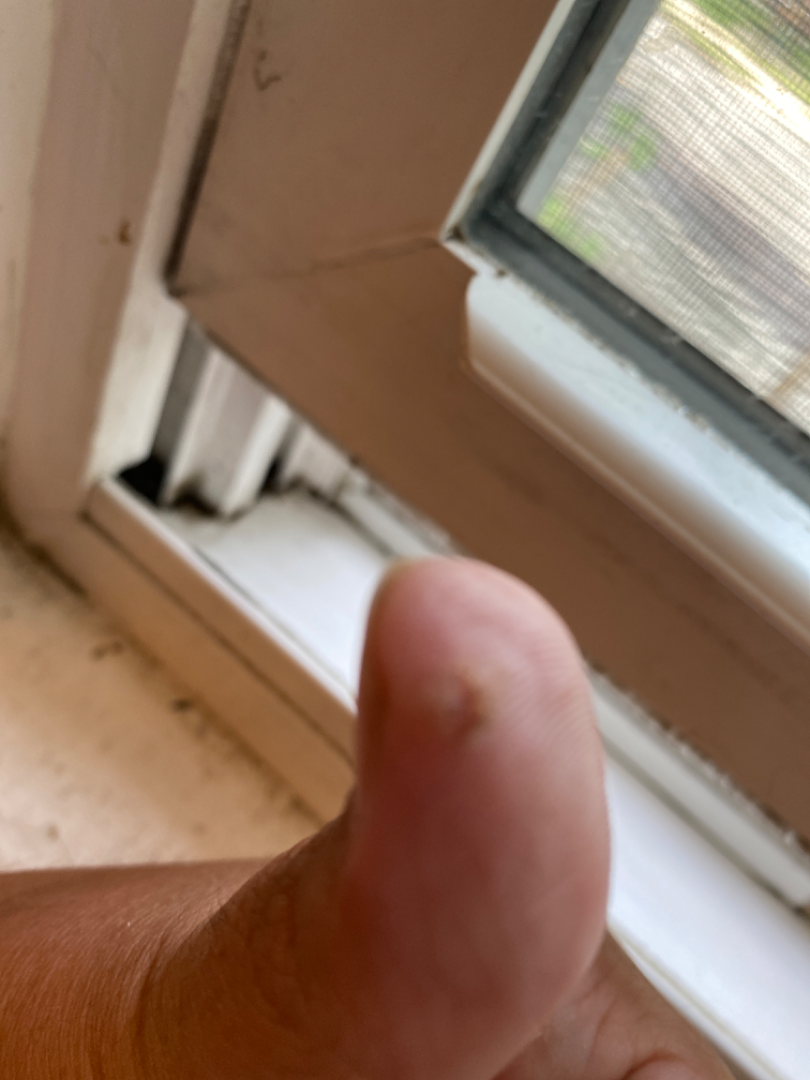Assessment:
The reviewing dermatologist was unable to assign a differential diagnosis from the image.
Clinical context:
A close-up photograph.